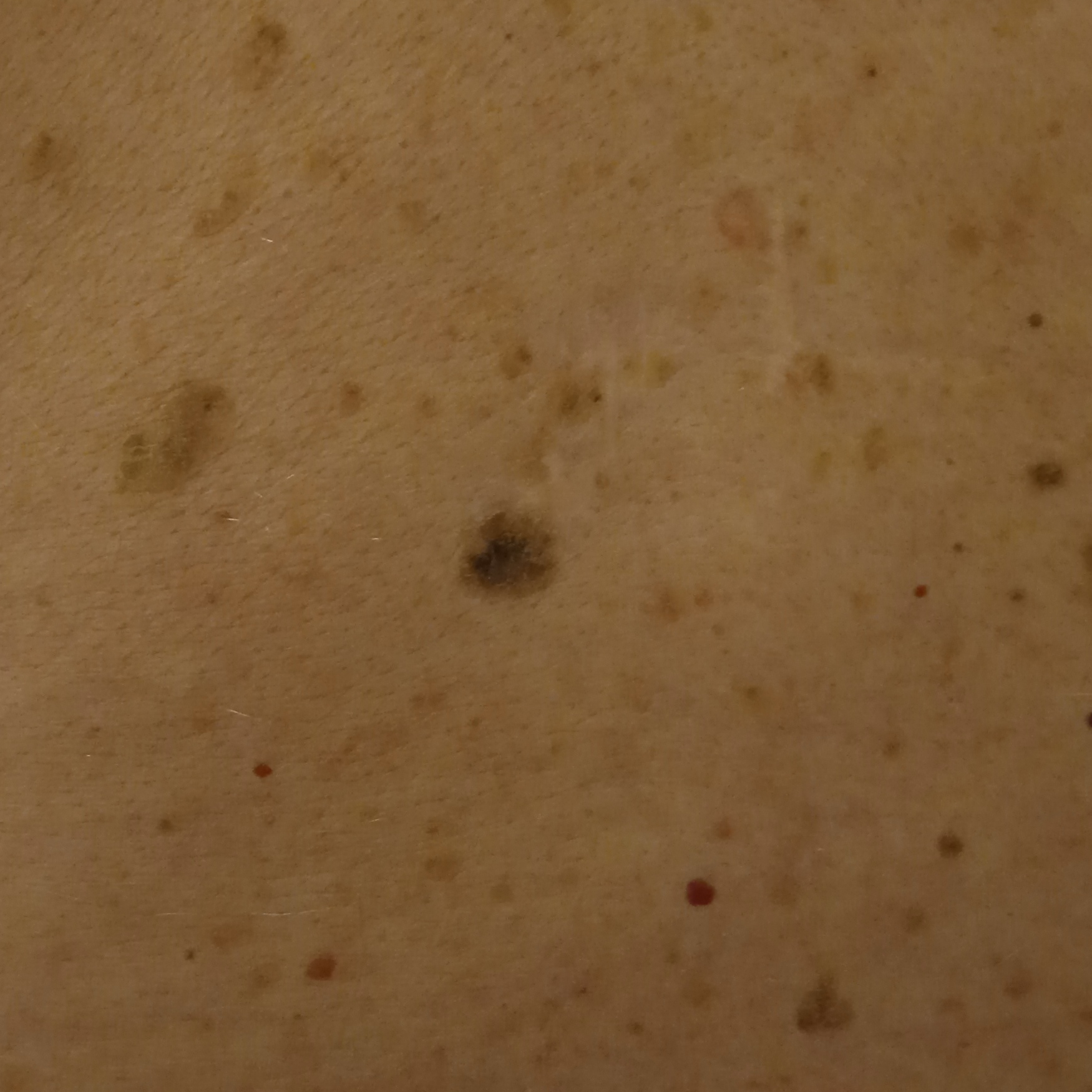A male subject 78 years of age.
Acquired for a research image collection, with no referral diagnosis.
A clinical close-up of a skin lesion.
Located on the back.
Measuring roughly 11 mm.
The lesion was assessed as a seborrheic keratosis.